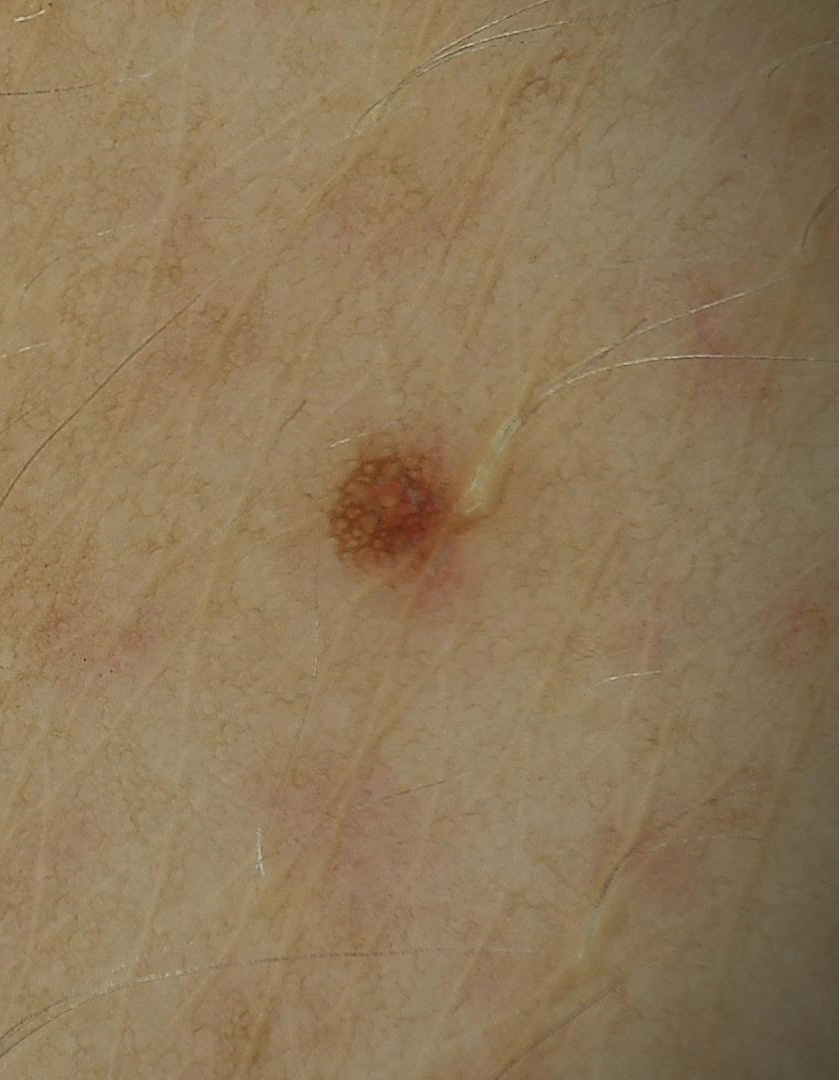Classified as a junctional nevus.